A dermoscopy image of a single skin lesion:
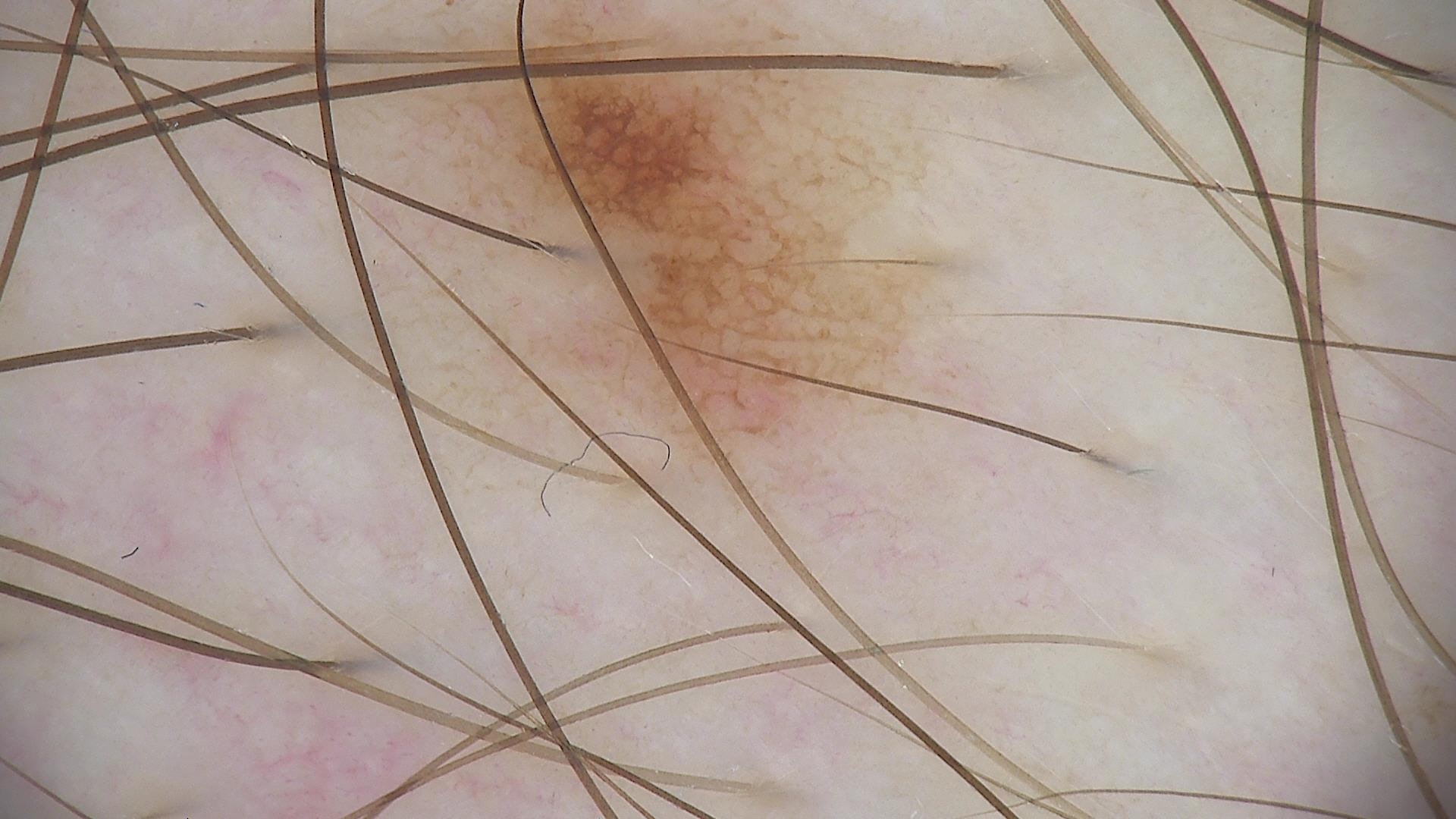The diagnosis was a dysplastic junctional nevus.